The patient notes the lesion is raised or bumpy; symptoms reported: pain, itching and burning; the patient notes associated joint pain and fatigue; the contributor is a female aged 50–59; the lesion involves the front of the torso; the patient notes the condition has been present for less than one week; the photo was captured at a distance:
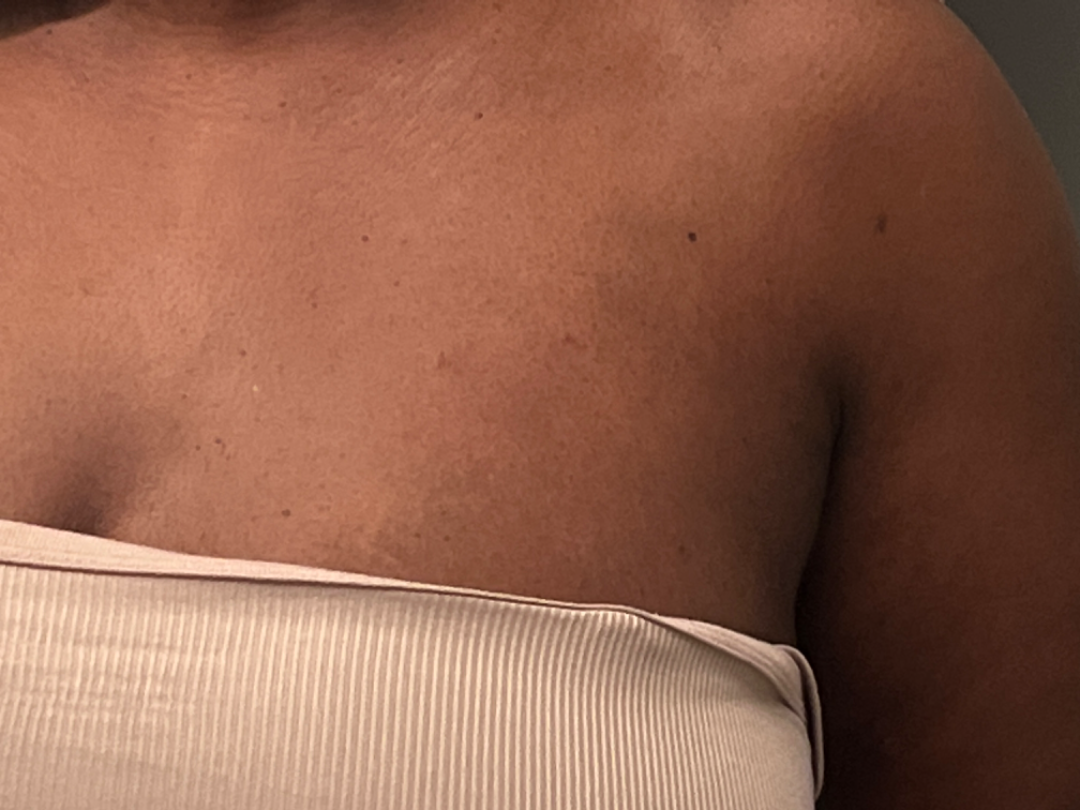The reviewing dermatologists' impression was: Tinea Versicolor (0.50); Post-Inflammatory hypopigmentation (0.50).